Dermoscopy of a skin lesion:
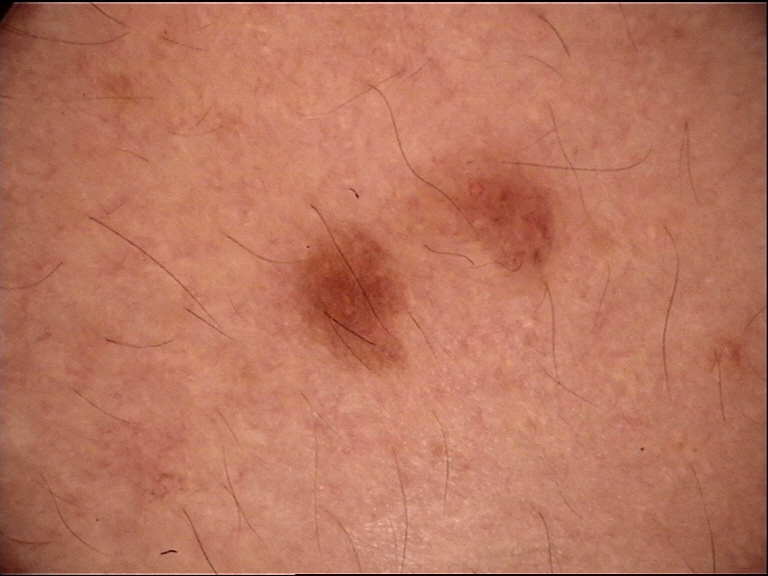This is a banal lesion. Consistent with a junctional nevus.